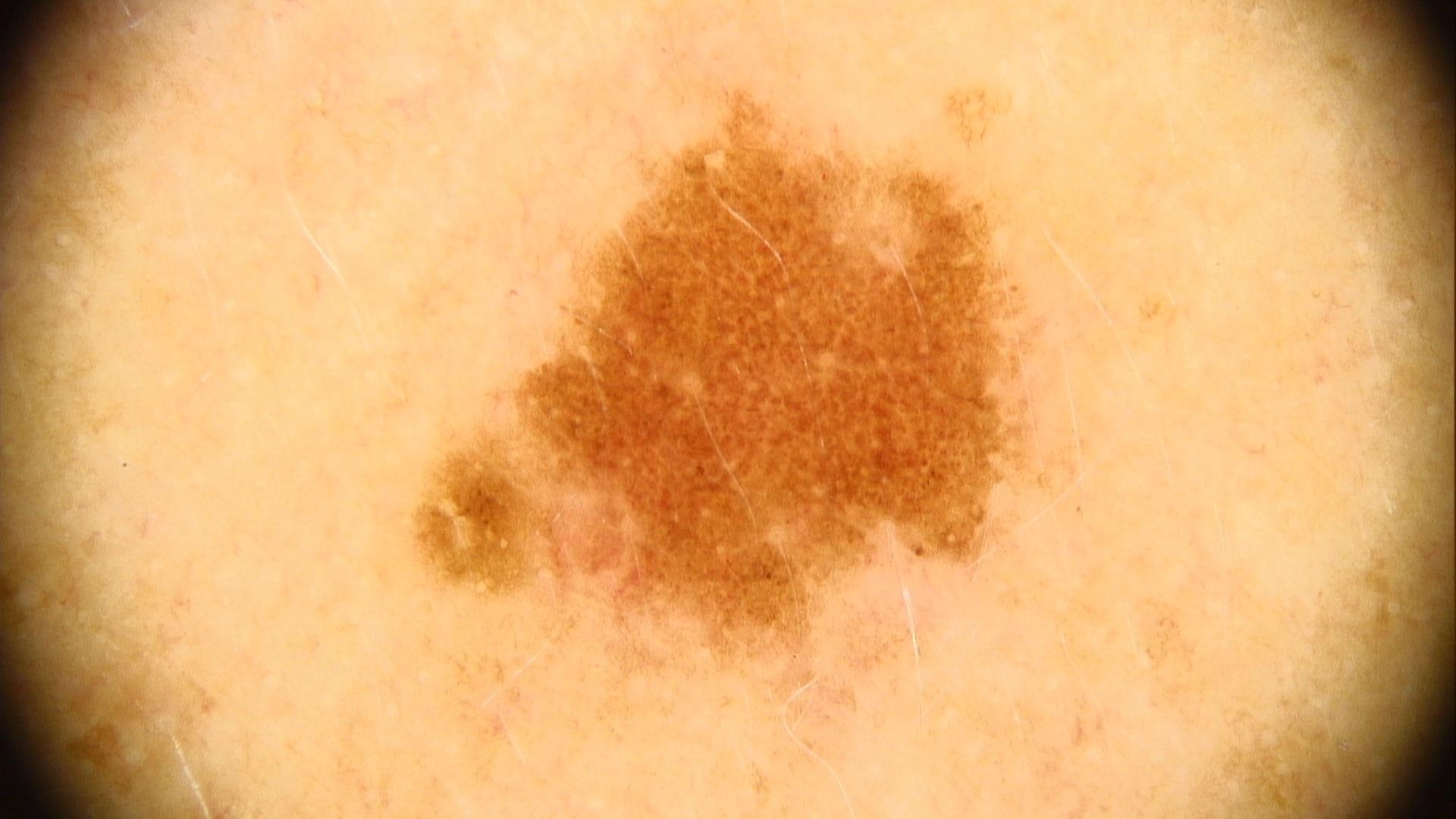image type: contact-polarized dermoscopy | patient: male, in their 40s | melanoma history: a first-degree relative with melanoma but no previous melanoma | Fitzpatrick: III | body site: the trunk, specifically the posterior trunk | diagnosis: Nevus (clinical impression).